Present for about one day; the patient reported no systemic symptoms; the patient indicates the lesion is raised or bumpy; the patient indicates itching; the contributor is 40–49, female; the back of the torso and front of the torso are involved; this is a close-up image:
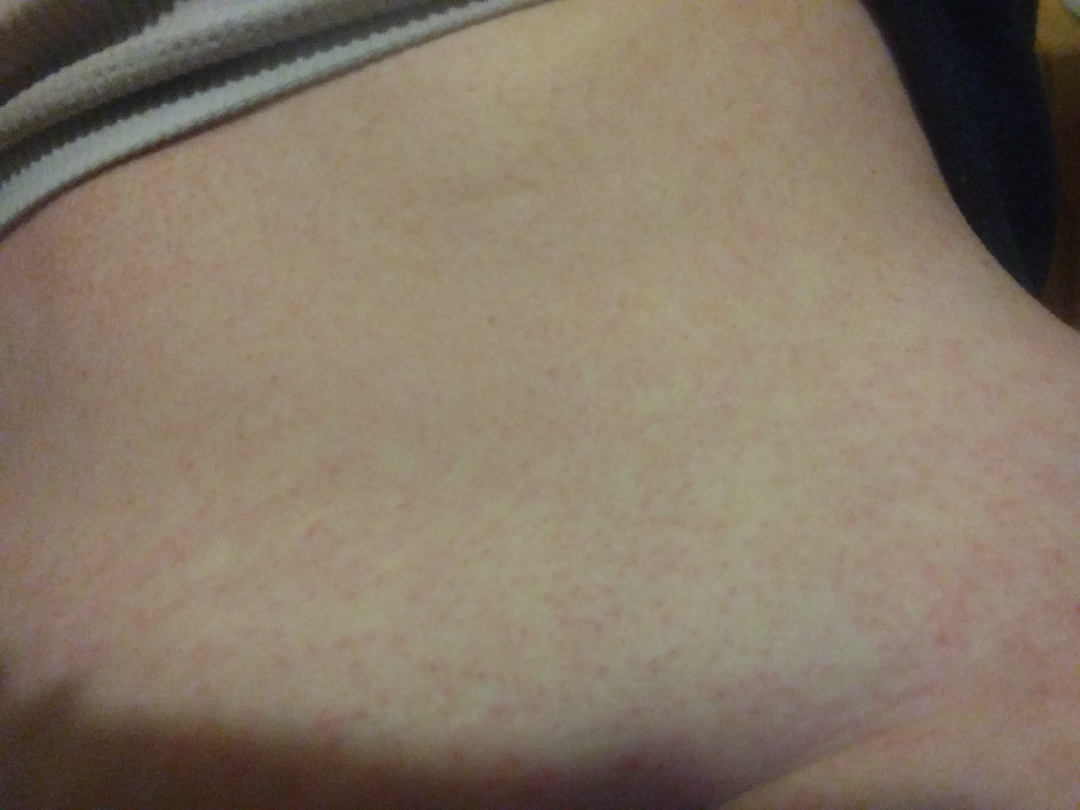clinical impression=the differential, in no particular order, includes Drug Rash, Viral Exanthem and Hypersensitivity